A subject in their late 50s · a clinical photo of a skin lesion taken with a smartphone.
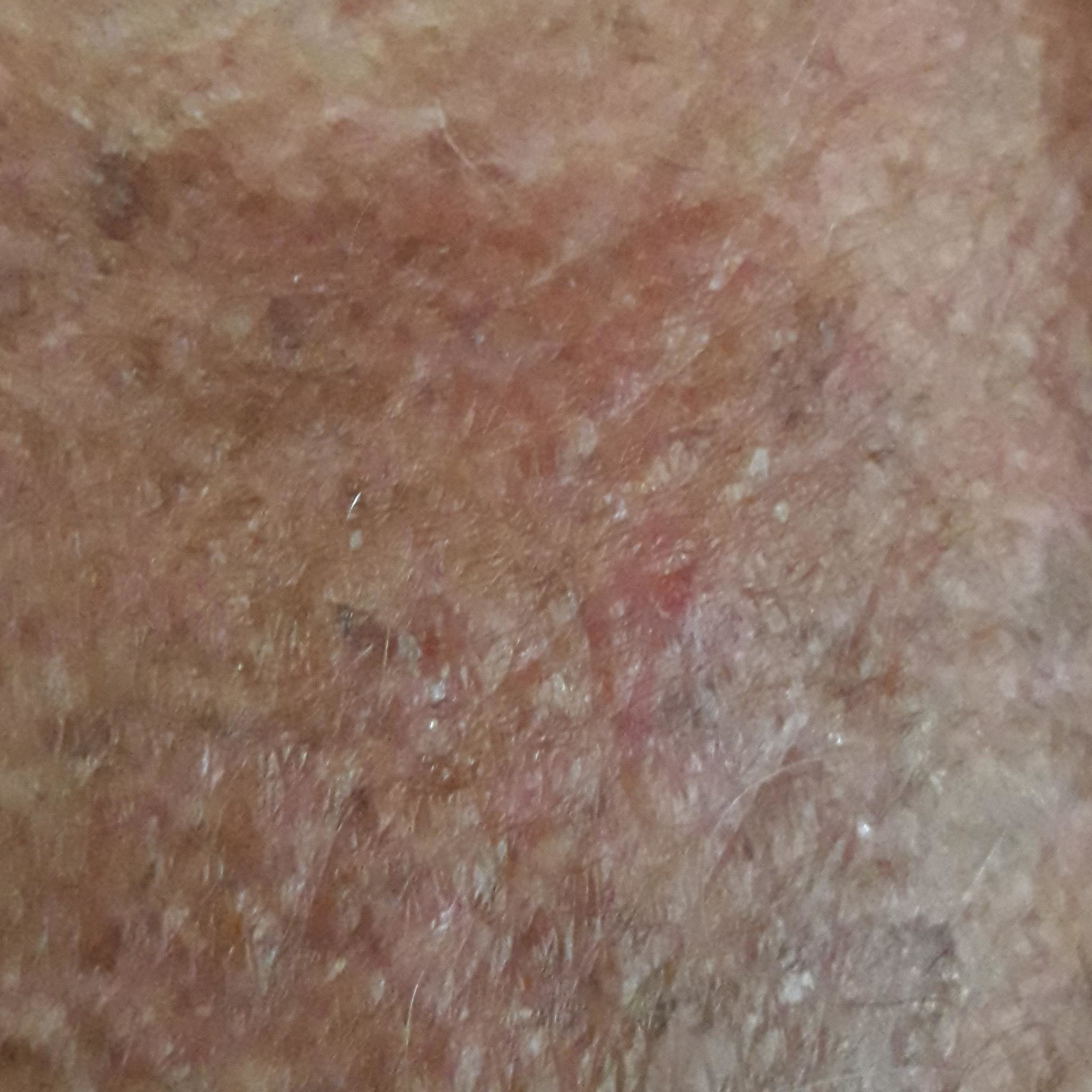anatomic site = a forearm; symptoms = none reported; impression = actinic keratosis (clinical consensus).